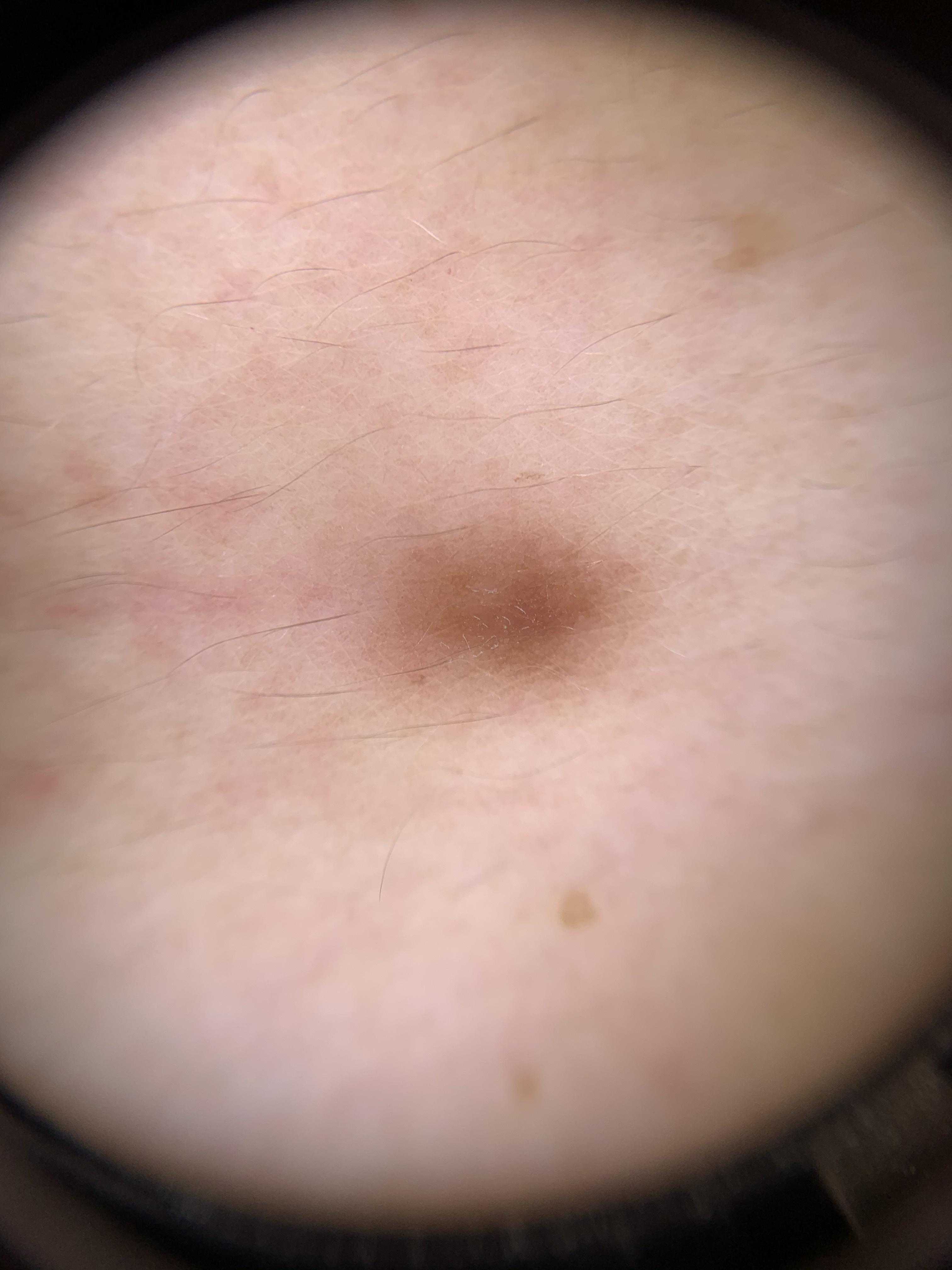Image and clinical context:
A contact-polarized dermoscopy image of a skin lesion. A female patient aged 43 to 47. The lesion was found on the trunk, specifically the anterior trunk.
Impression:
Expert review favored a dermatofibroma.